A subject in their late 70s · a clinical close-up photograph of a skin lesion:
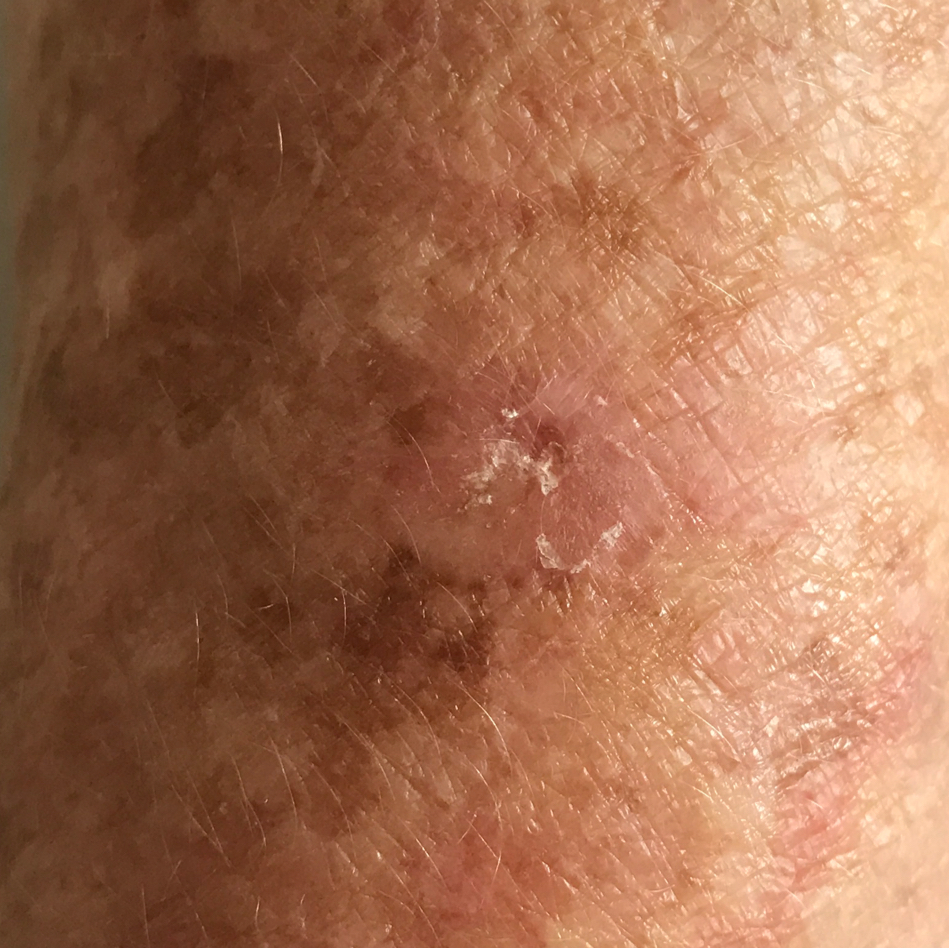The patient describes that the lesion is elevated and itches. The clinical impression was an actinic keratosis.